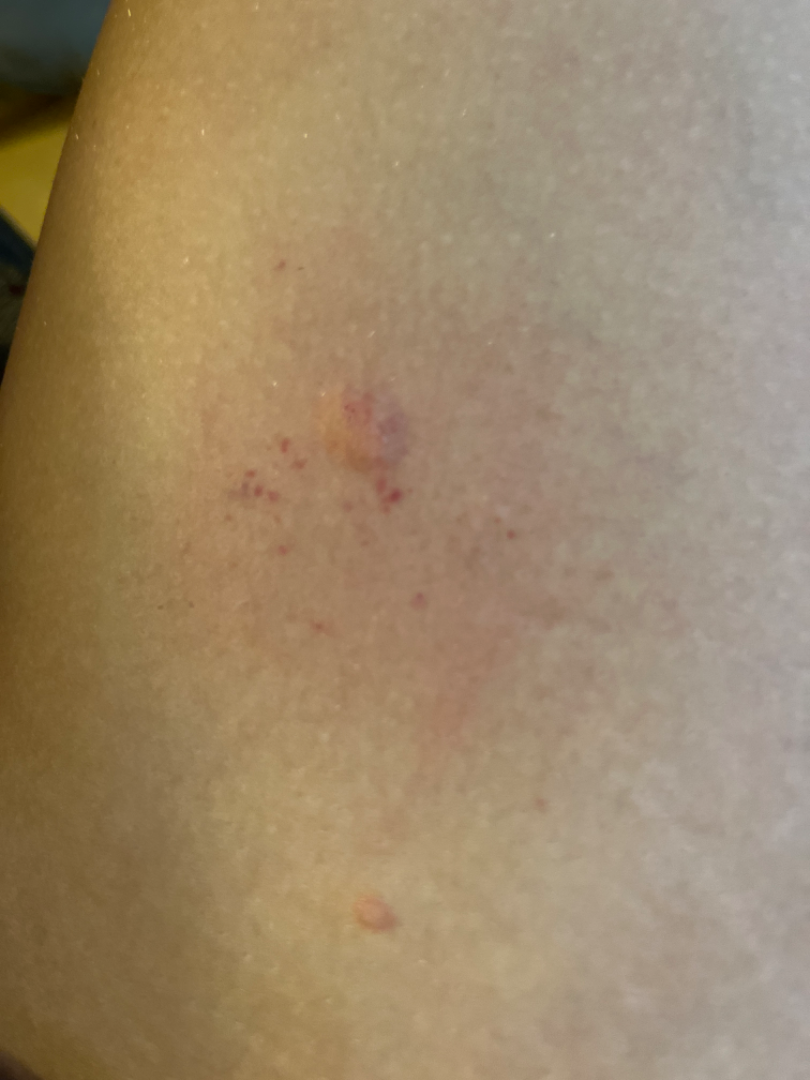impression = Verruca vulgaris and SCC/SCCIS were considered with similar weight.